The lesion involves the arm. The patient is a male aged 30–39. The photo was captured at an angle: 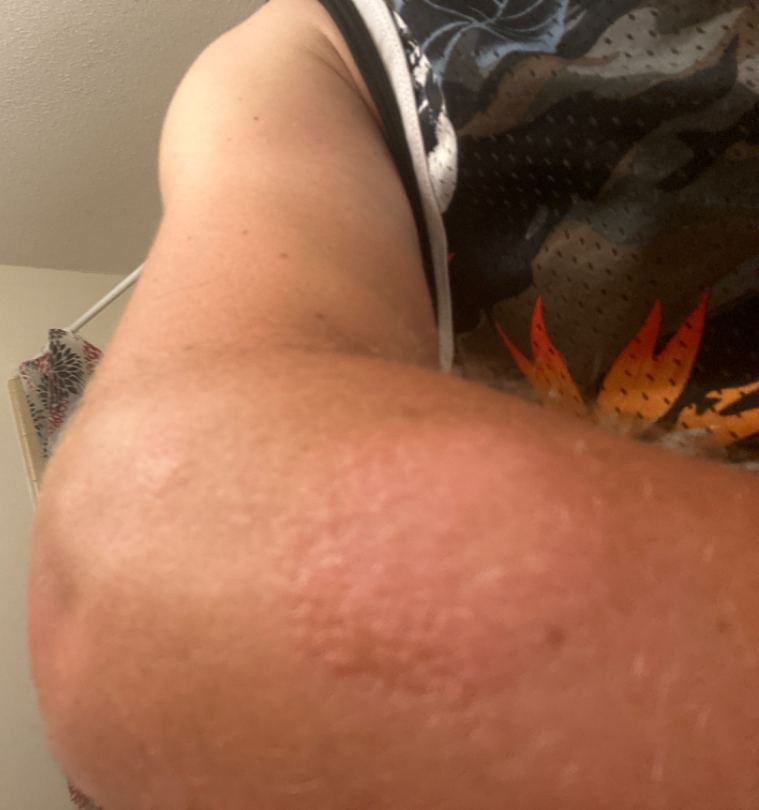The patient described the issue as a rash. Associated systemic symptoms include chills, fatigue, mouth sores and joint pain. The condition has been present for one to four weeks. The lesion is associated with itching, bothersome appearance and enlargement. The patient notes the lesion is raised or bumpy. Skin tone: Fitzpatrick III; human graders estimated MST 3 or 4. On photographic review: the leading consideration is Tinea.